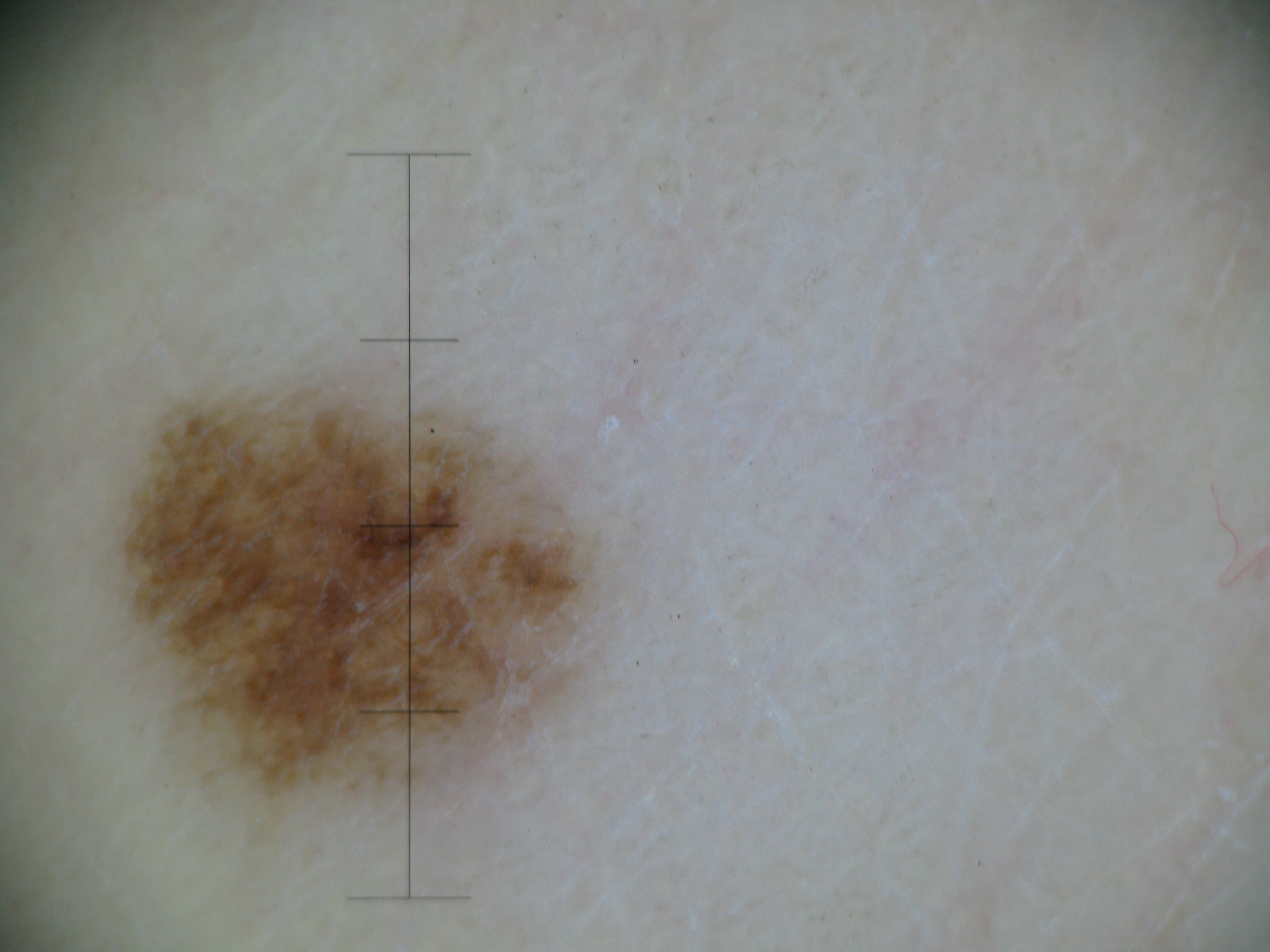A dermoscopic image of a skin lesion. This is a banal lesion. The diagnostic label was a compound nevus.